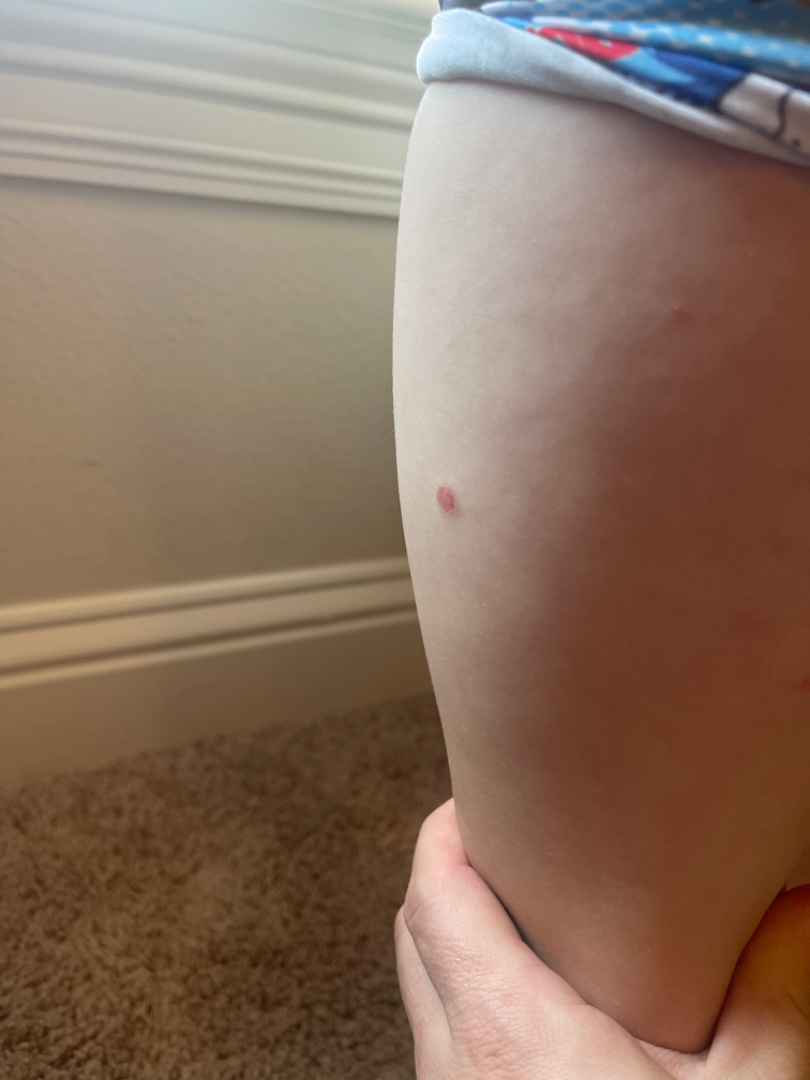impression: Hemangioma (considered); Melanocytic Nevus (considered); Pyogenic granuloma (considered)